A dermatoscopic image of a skin lesion:
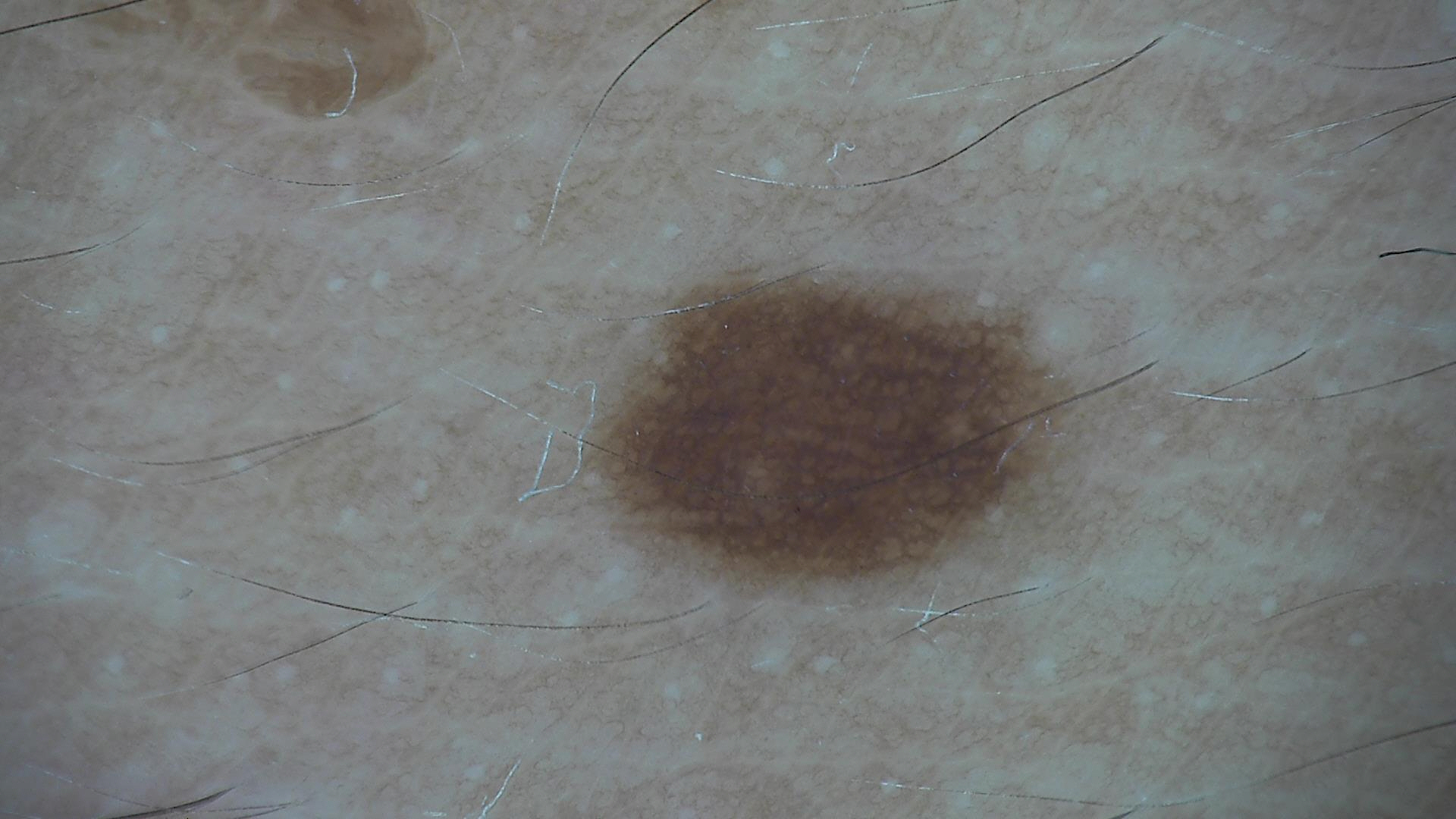Consistent with a dysplastic junctional nevus.